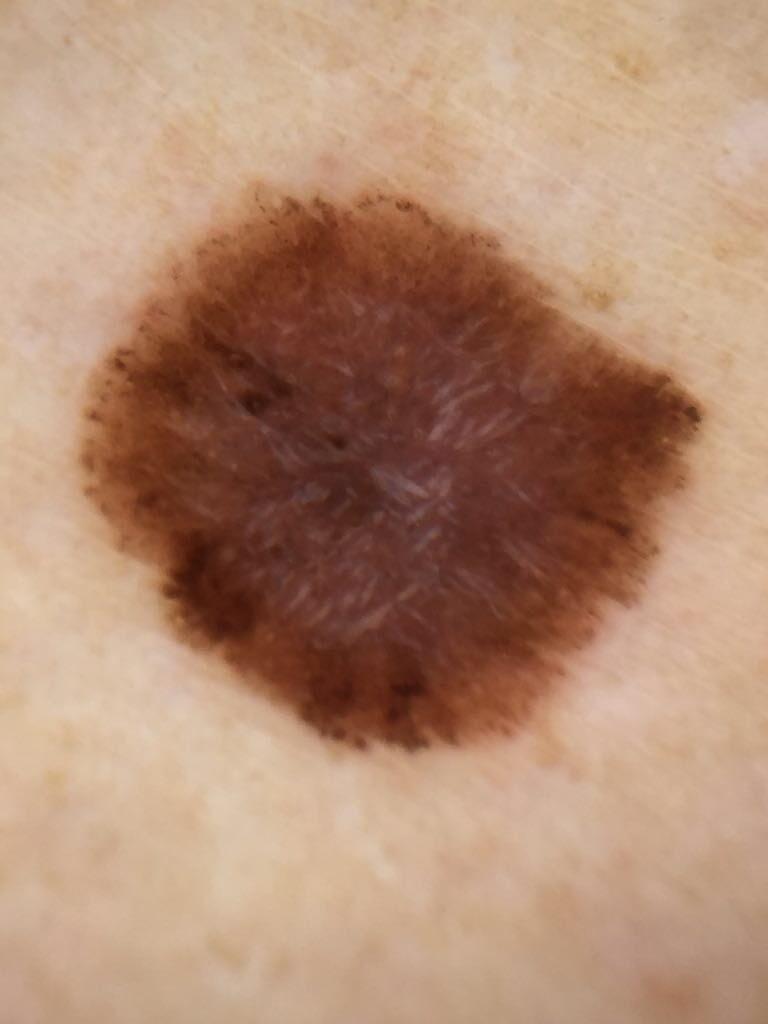Case:
- diagnosis · Melanoma (biopsy-proven)